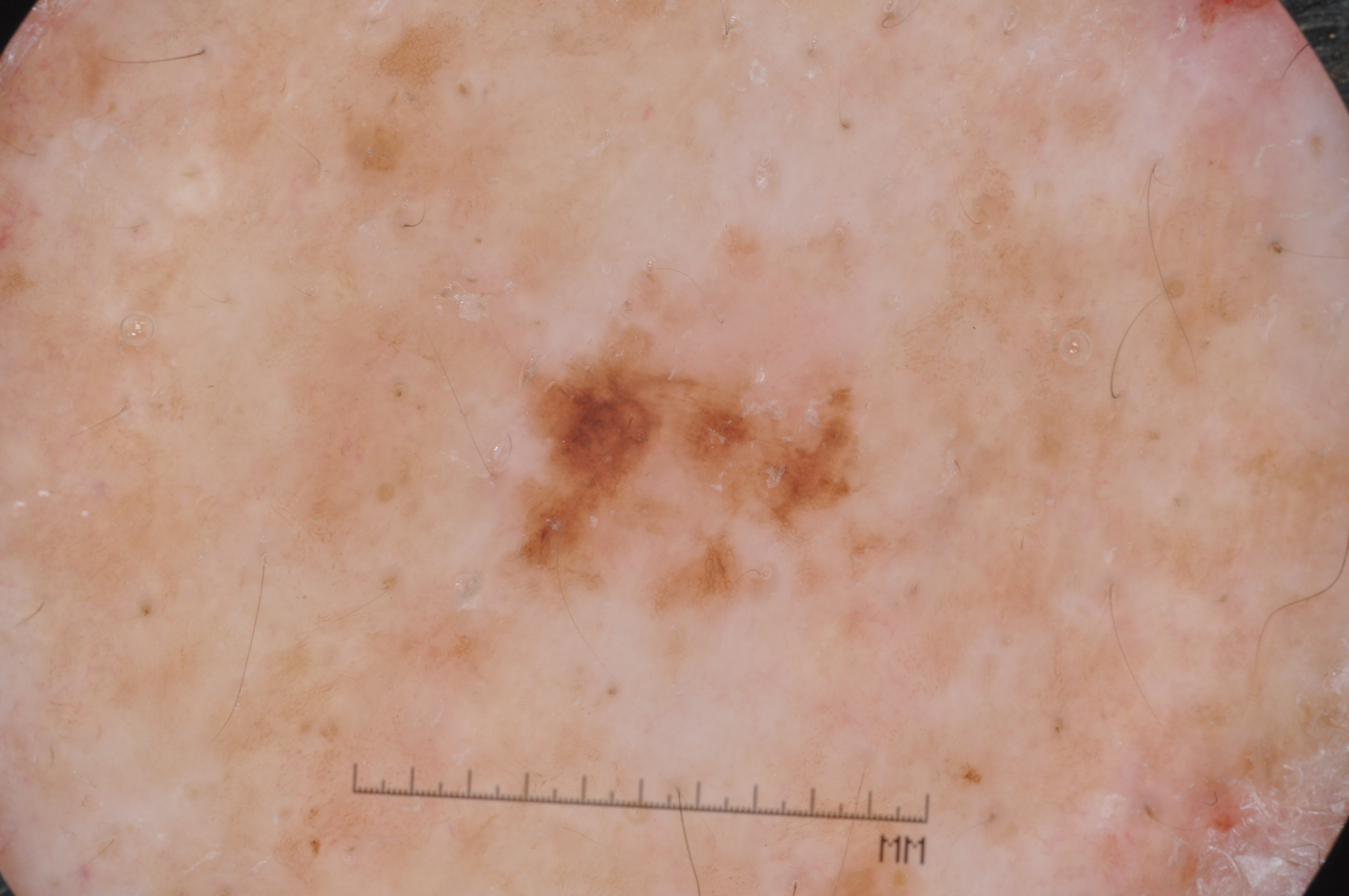Q: How was this image acquired?
A: dermoscopy
Q: Lesion extent?
A: moderate
Q: What is the lesion's bounding box?
A: 471 205 903 646
Q: What does dermoscopy show?
A: pigment network; absent: streaks, negative network, and milia-like cysts
Q: What is this lesion?
A: a melanocytic nevus